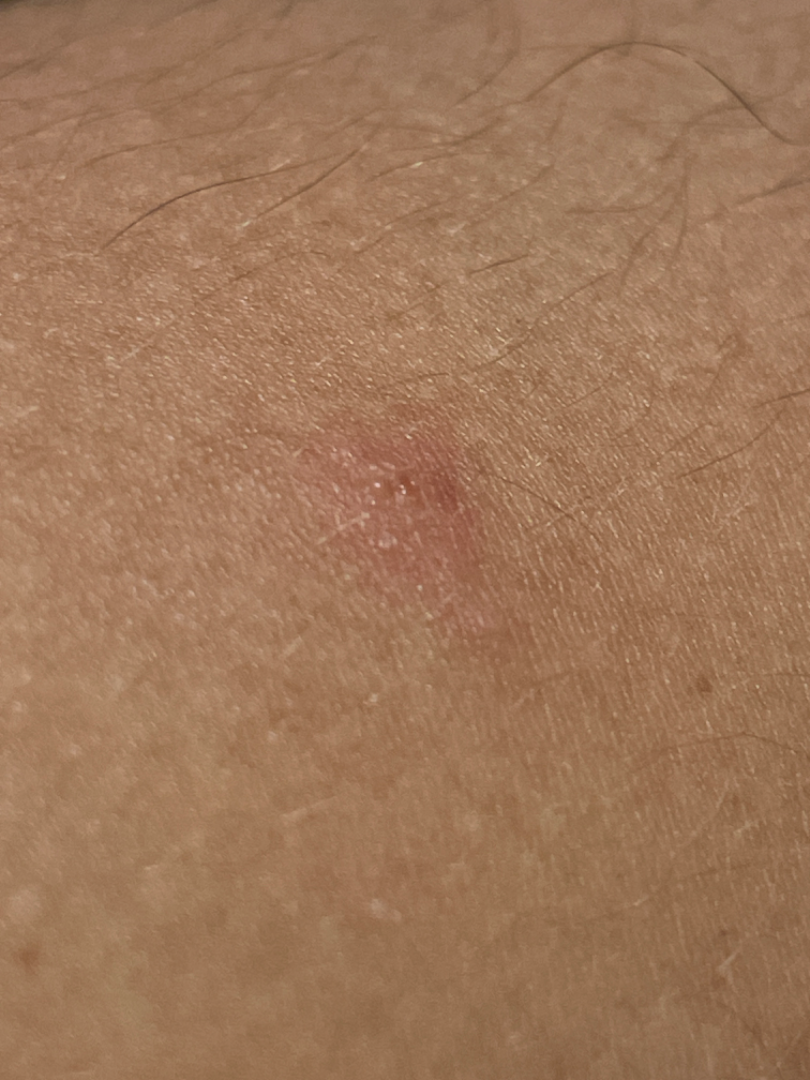Findings:
- surface texture · fluid-filled and raised or bumpy
- body site · arm
- reported symptoms · itching, burning, bothersome appearance and darkening
- self-categorized as · a rash
- skin tone · human graders estimated MST 6 (US pool) or 4 (India pool)
- view · close-up
- impression · Impetigo, Insect Bite and Allergic Contact Dermatitis were each considered, in no particular order